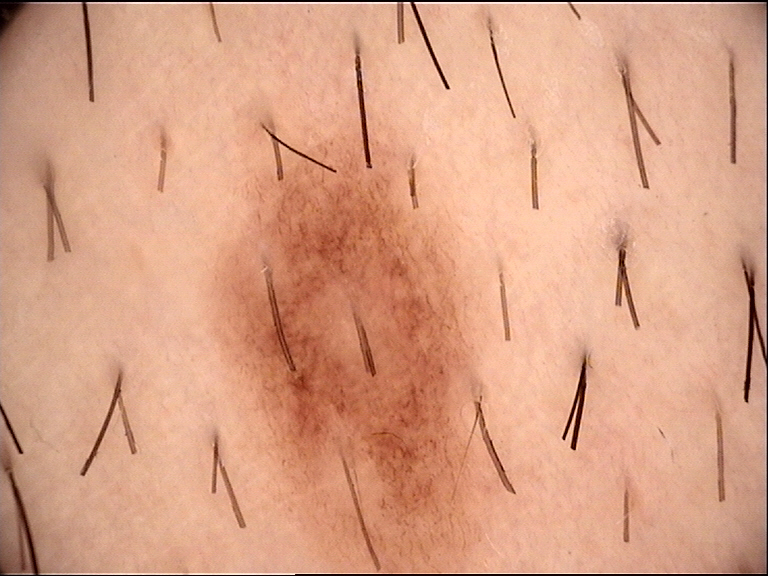A dermoscopic image of a skin lesion. Consistent with a dysplastic junctional nevus.